The patient says their skin reddens with sun exposure; by self-report, a prior organ transplant; a male subject aged 66; collected as part of a research study, without a referral diagnosis; a clinical photograph of a skin lesion:
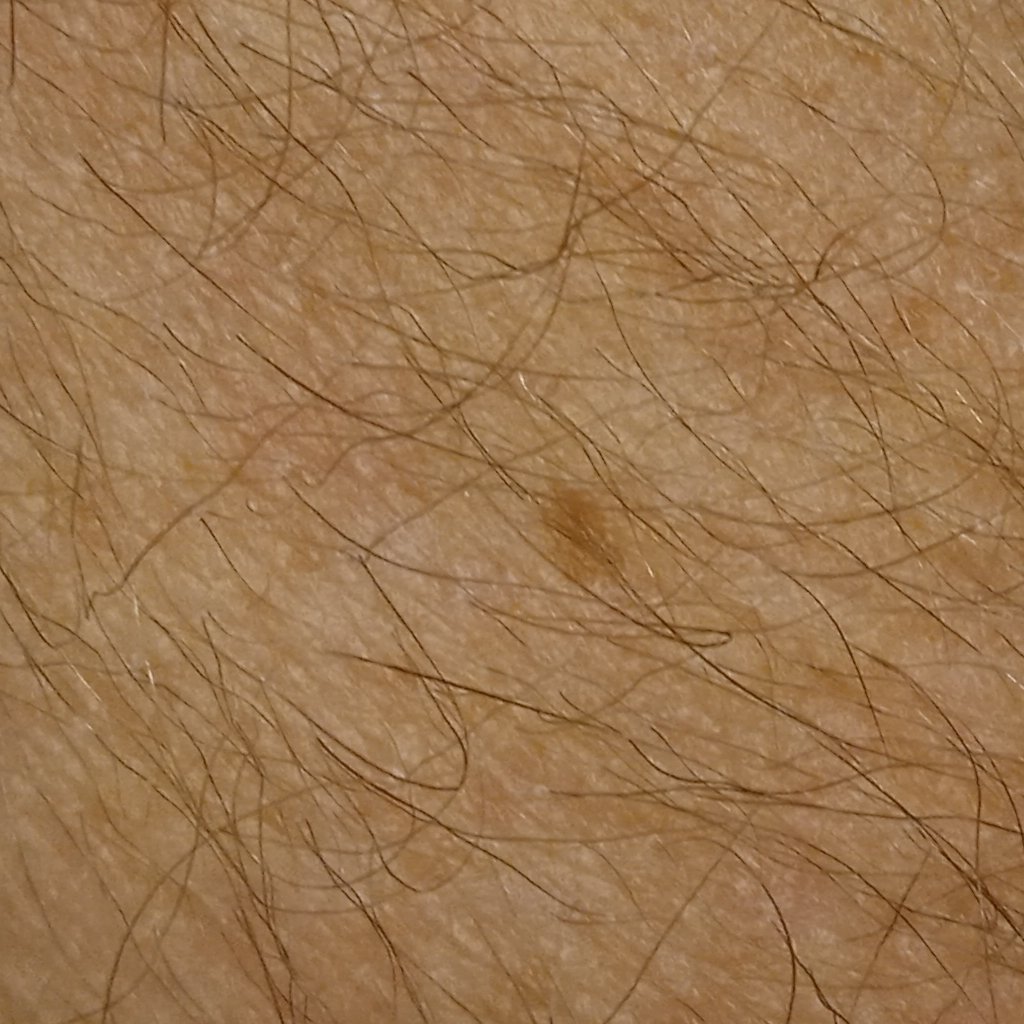lesion_location: an arm
diagnosis:
  name: melanocytic nevus
  malignancy: benign